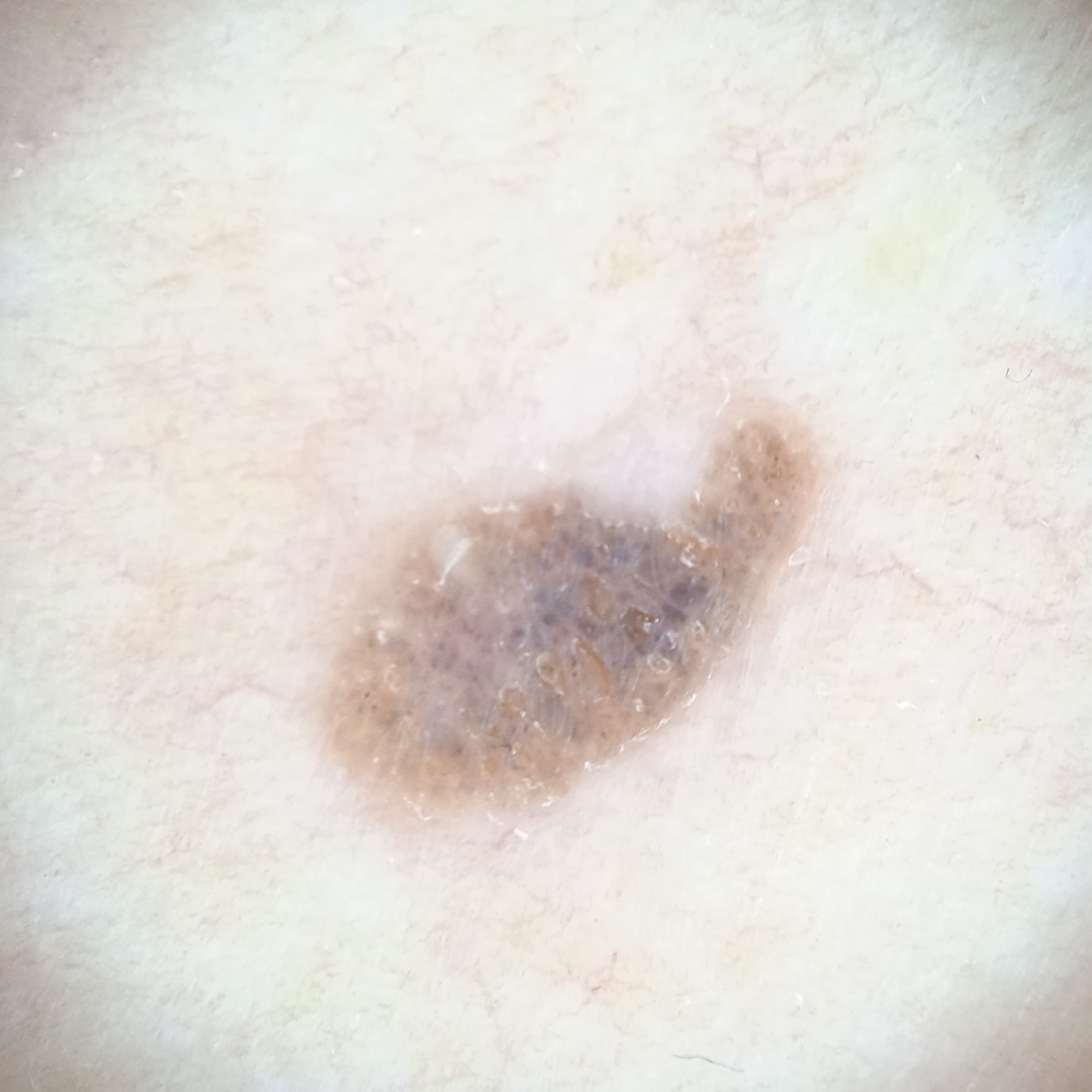A skin lesion imaged with a dermatoscope.
By self-report, a personal history of cancer and a personal history of skin cancer.
A female patient 60 years of age.
The patient says their skin tans without first burning.
Acquired for a research image collection, with no referral diagnosis.
Few moles overall by the patient's own estimate.
The lesion is on the torso.
The consensus diagnosis for this lesion was a seborrheic keratosis.